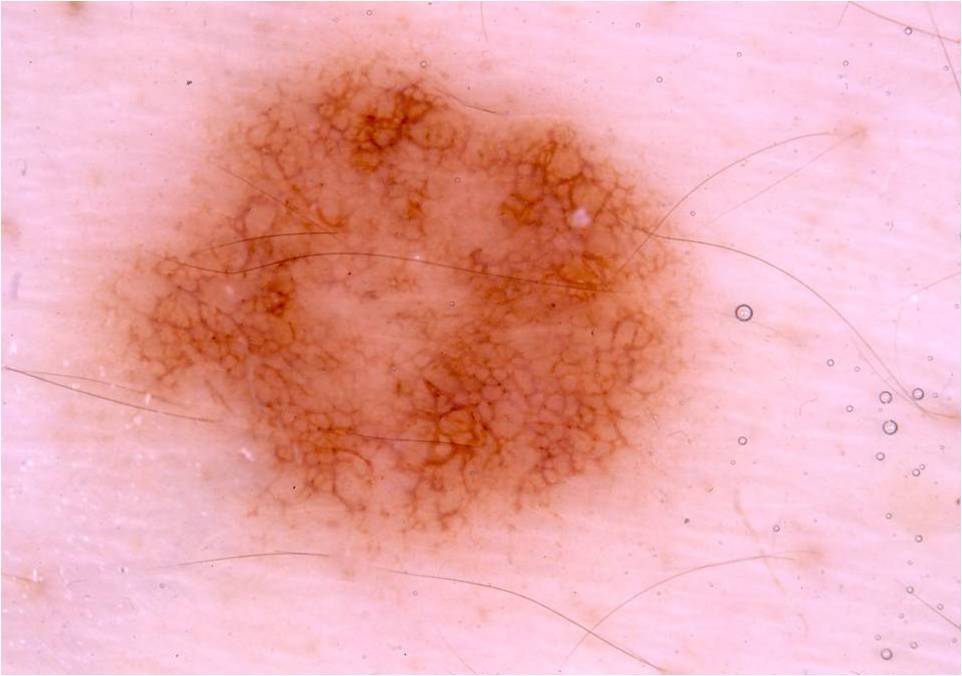{"patient": {"sex": "male", "age_approx": 20}, "image": {"modality": "dermoscopy"}, "lesion_location": {"bbox_xyxy": [79, 14, 733, 588]}, "dermoscopic_features": {"present": ["pigment network", "milia-like cysts"], "absent": ["globules", "streaks", "negative network"]}, "diagnosis": {"name": "melanocytic nevus", "malignancy": "benign", "lineage": "melanocytic", "provenance": "clinical"}}